A male patient, about 50 years old · dermoscopy of a skin lesion.
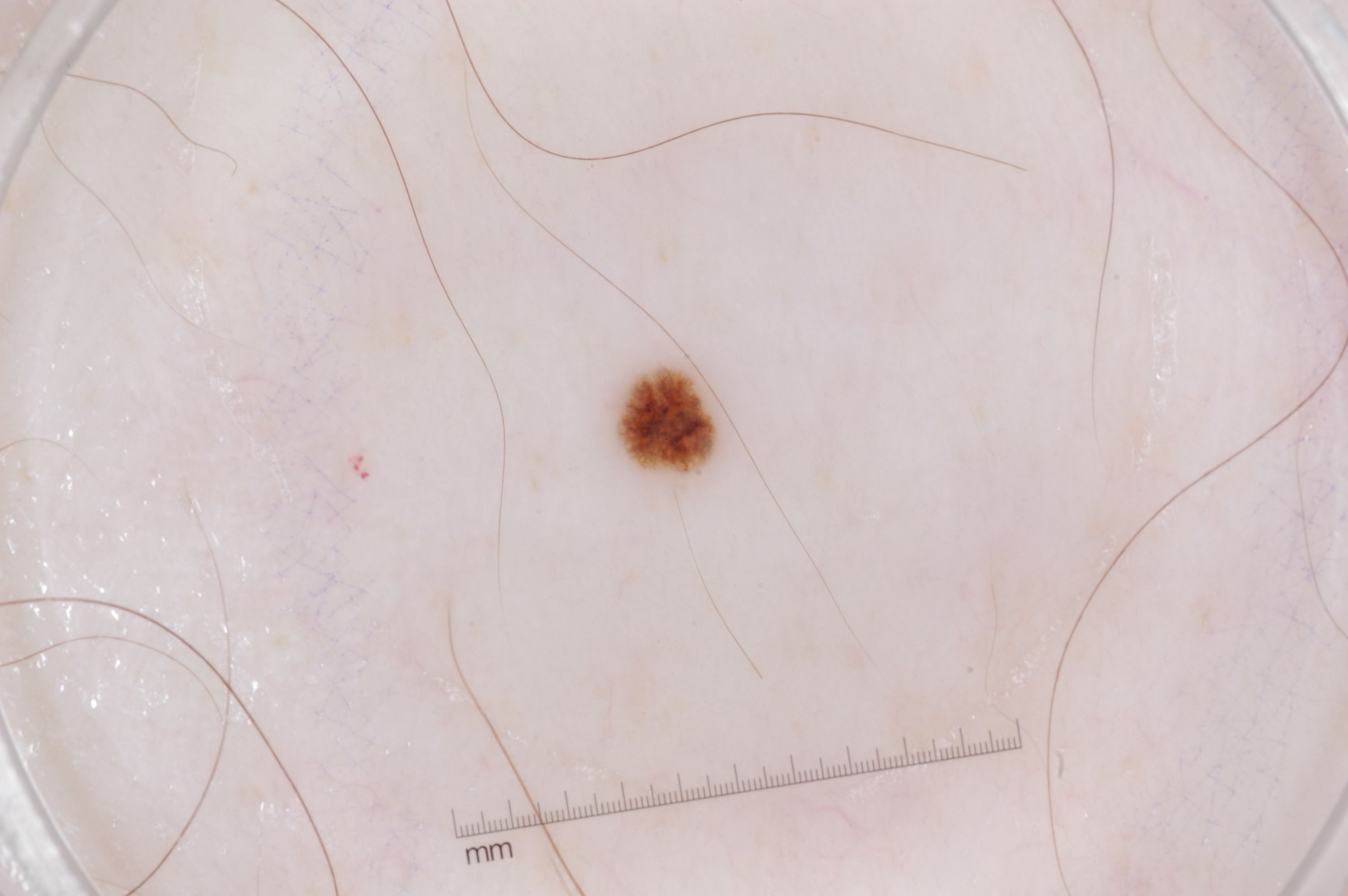location = x1=611, y1=357, x2=726, y2=476 | dermoscopic findings = pigment network | extent = ~1% of the field | assessment = a melanocytic nevus.